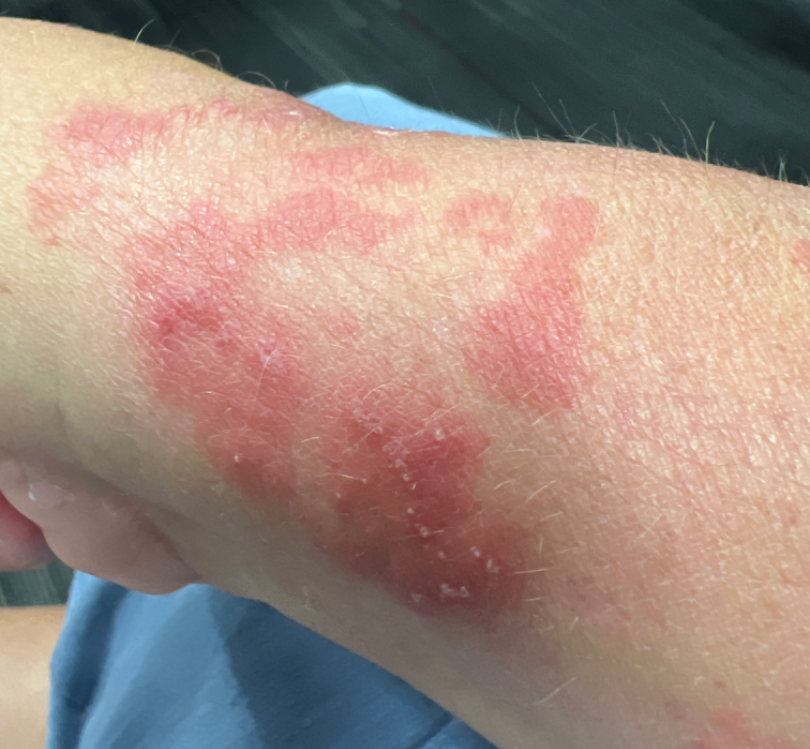On remote dermatologist review, the reviewer's impression was Acute dermatitis, NOS.